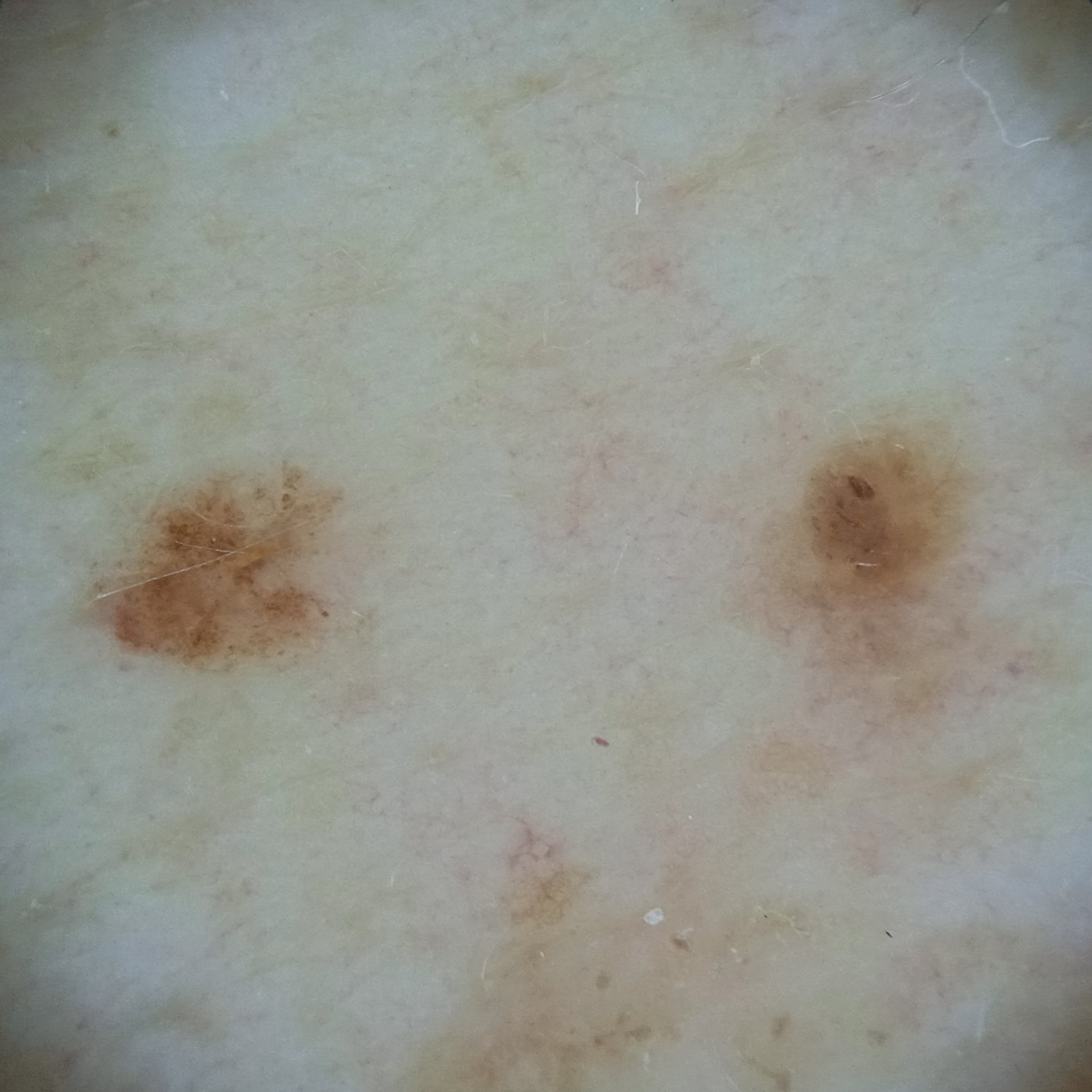Findings:
The patient says their skin reddens with sun exposure. A male patient age 78. The patient reports a personal history of cancer and no personal history of skin cancer. Few moles overall by the patient's own estimate. A dermoscopy image of a skin lesion. Located on the back. Measuring roughly 3.1 mm.
Impression:
The dermatologists' assessment was a seborrheic keratosis.